A male patient 51 years of age · a clinical photograph showing a skin lesion:
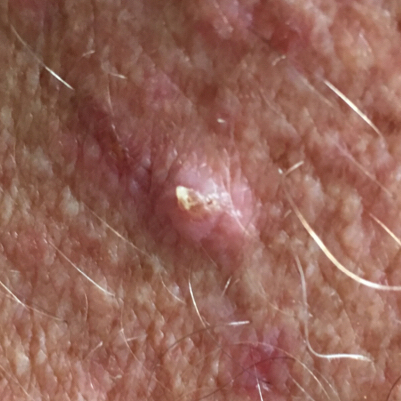Q: What are the lesion's dimensions?
A: 15 × 7 mm
Q: Any reported symptoms?
A: elevation, itching
Q: What is the diagnosis?
A: squamous cell carcinoma (biopsy-proven)